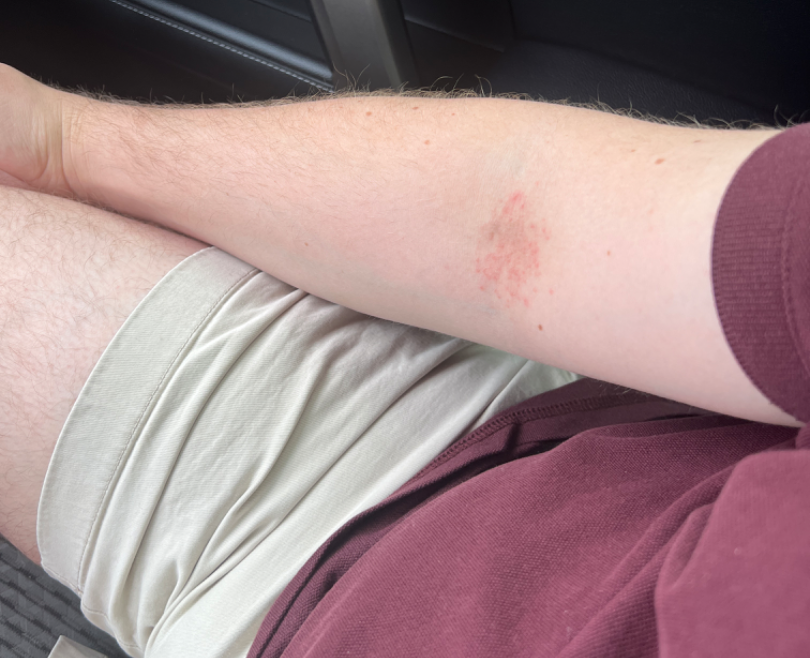Findings:
- assessment: most consistent with Eczema; less probable is Allergic Contact Dermatitis